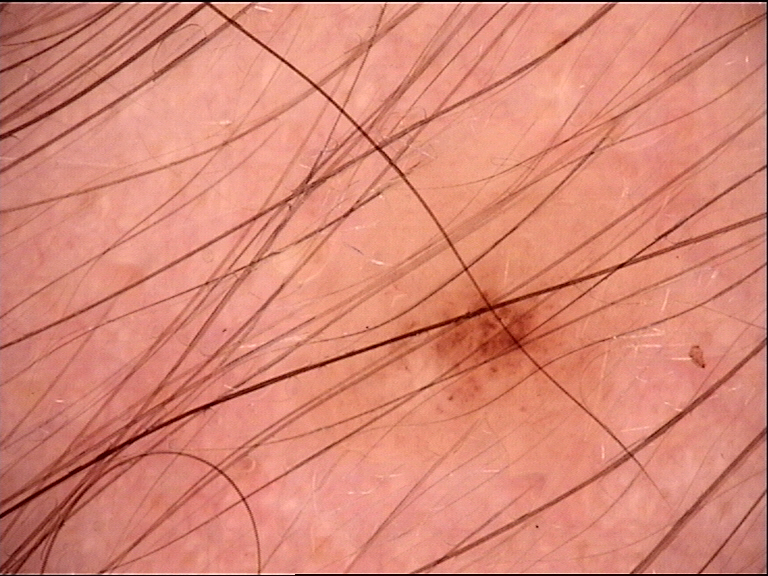image: dermatoscopy
diagnosis:
  name: dysplastic junctional nevus
  code: jd
  malignancy: benign
  super_class: melanocytic
  confirmation: expert consensus